The photograph was taken at an angle:
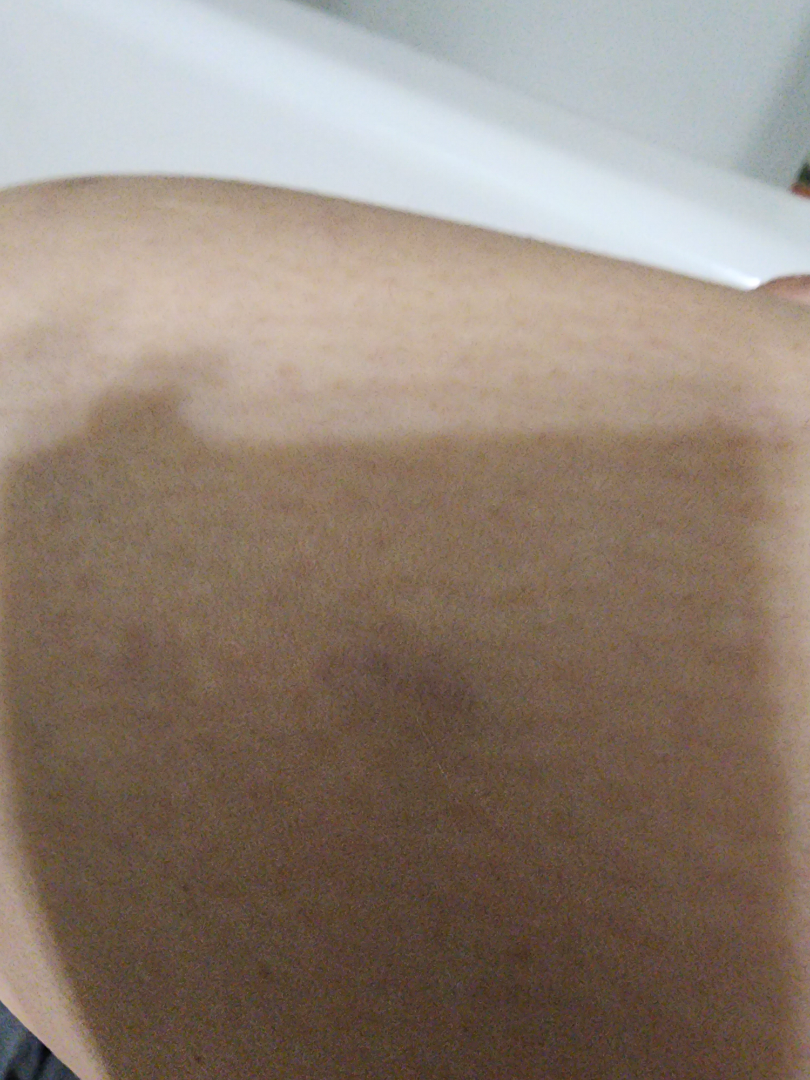The image was not sufficient for the reviewer to characterize the skin condition.